A dermoscopic close-up of a skin lesion · a female subject, aged around 80:
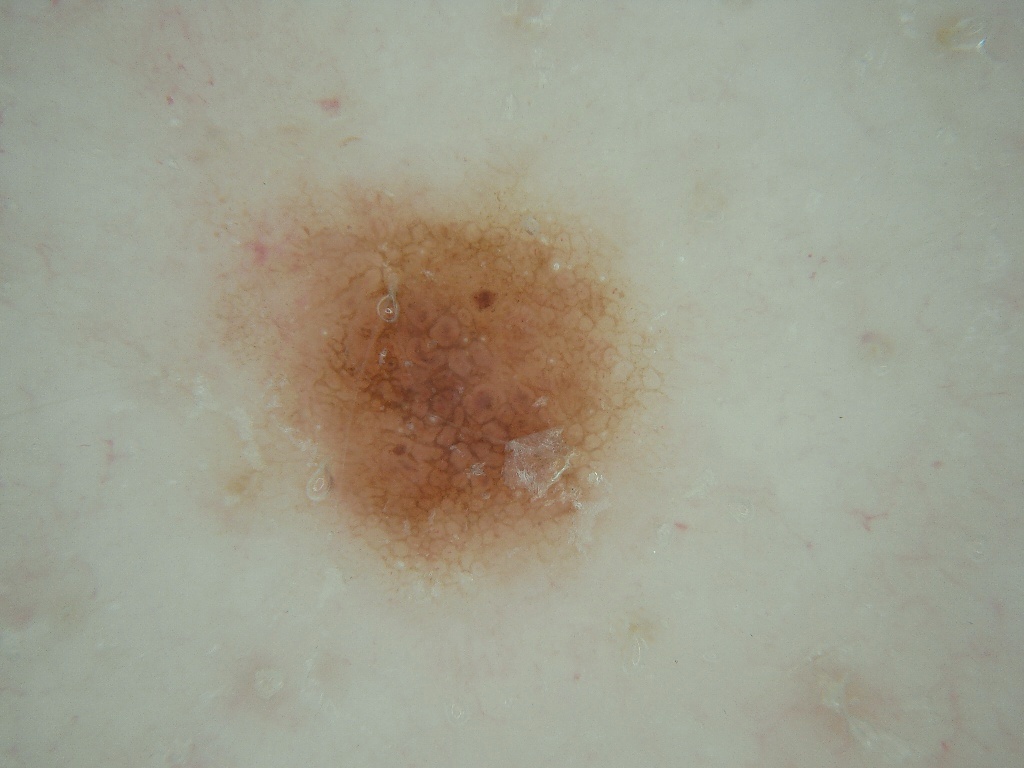Case summary: Dermoscopy demonstrates globules and pigment network, with no milia-like cysts, negative network, or streaks. A mid-sized lesion within the field. As (left, top, right, bottom), the visible lesion spans [171,159,673,604]. Conclusion: Clinically diagnosed as a melanocytic nevus, a benign lesion.